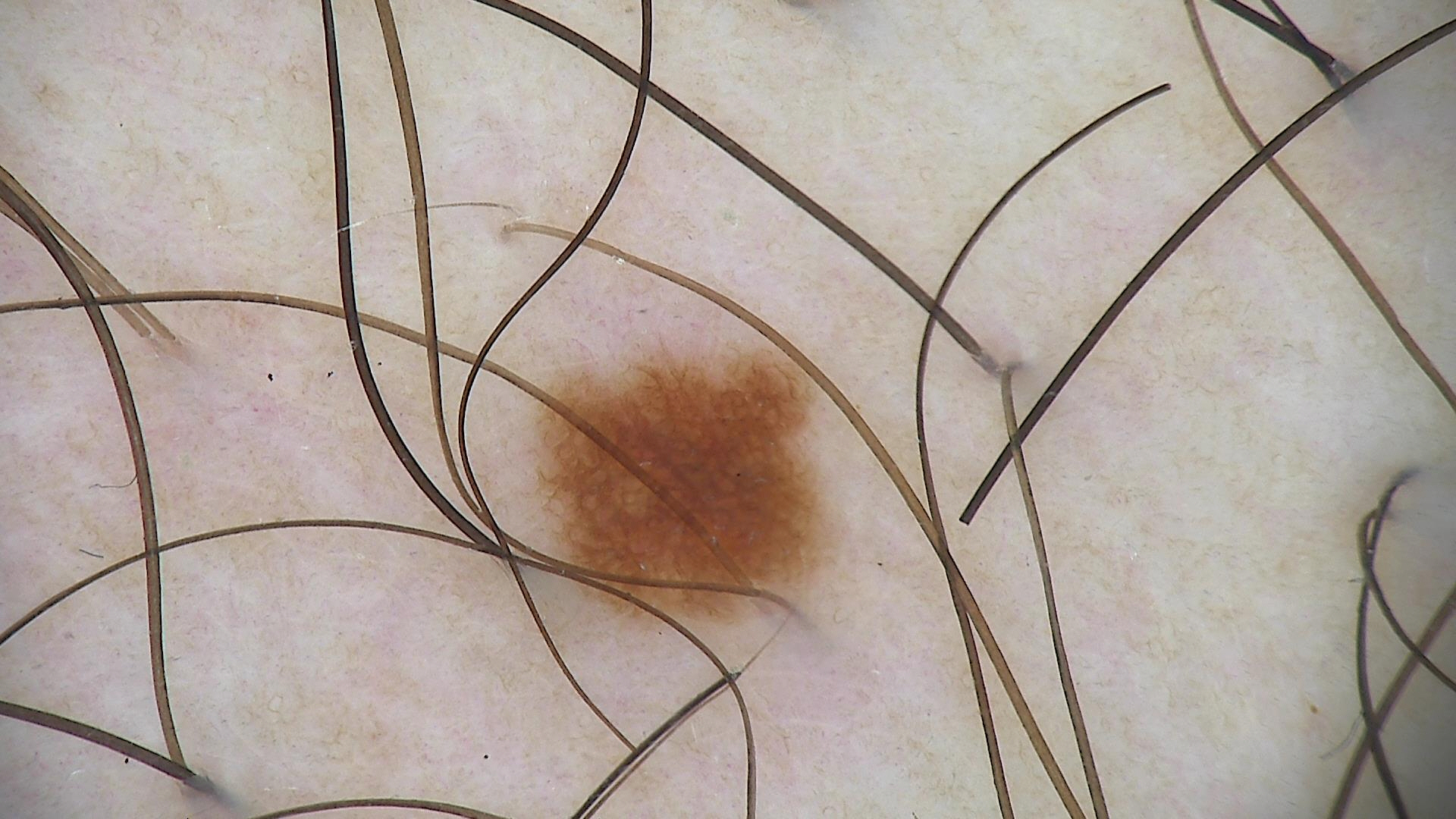– diagnostic label · dysplastic junctional nevus (expert consensus)